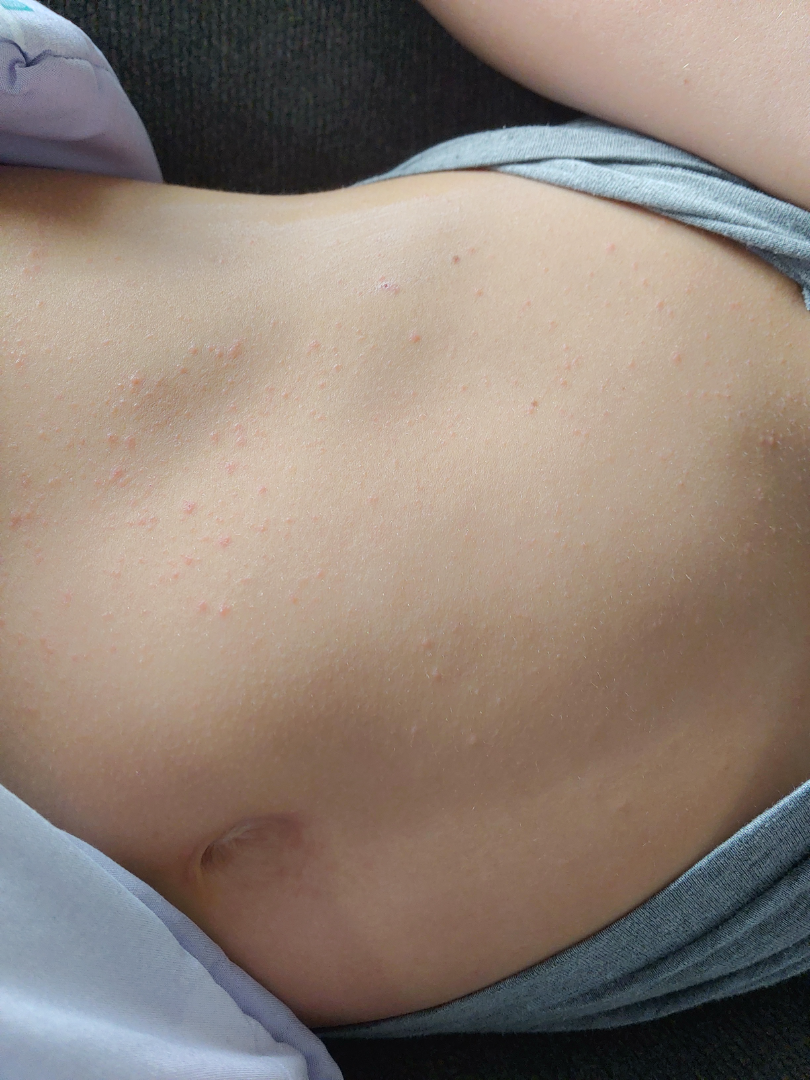Q: What was the assessment?
A: ungradable on photographic review
Q: What is the affected area?
A: arm, head or neck, front of the torso, back of the torso and back of the hand
Q: Texture?
A: raised or bumpy and rough or flaky
Q: How does the patient describe it?
A: skin that appeared healthy to them
Q: What is the patient's skin tone?
A: Fitzpatrick phototype II; lay reviewers estimated a Monk Skin Tone of 3
Q: Image view?
A: at a distance
Q: What symptoms does the patient report?
A: itching
Q: Any systemic symptoms?
A: none reported